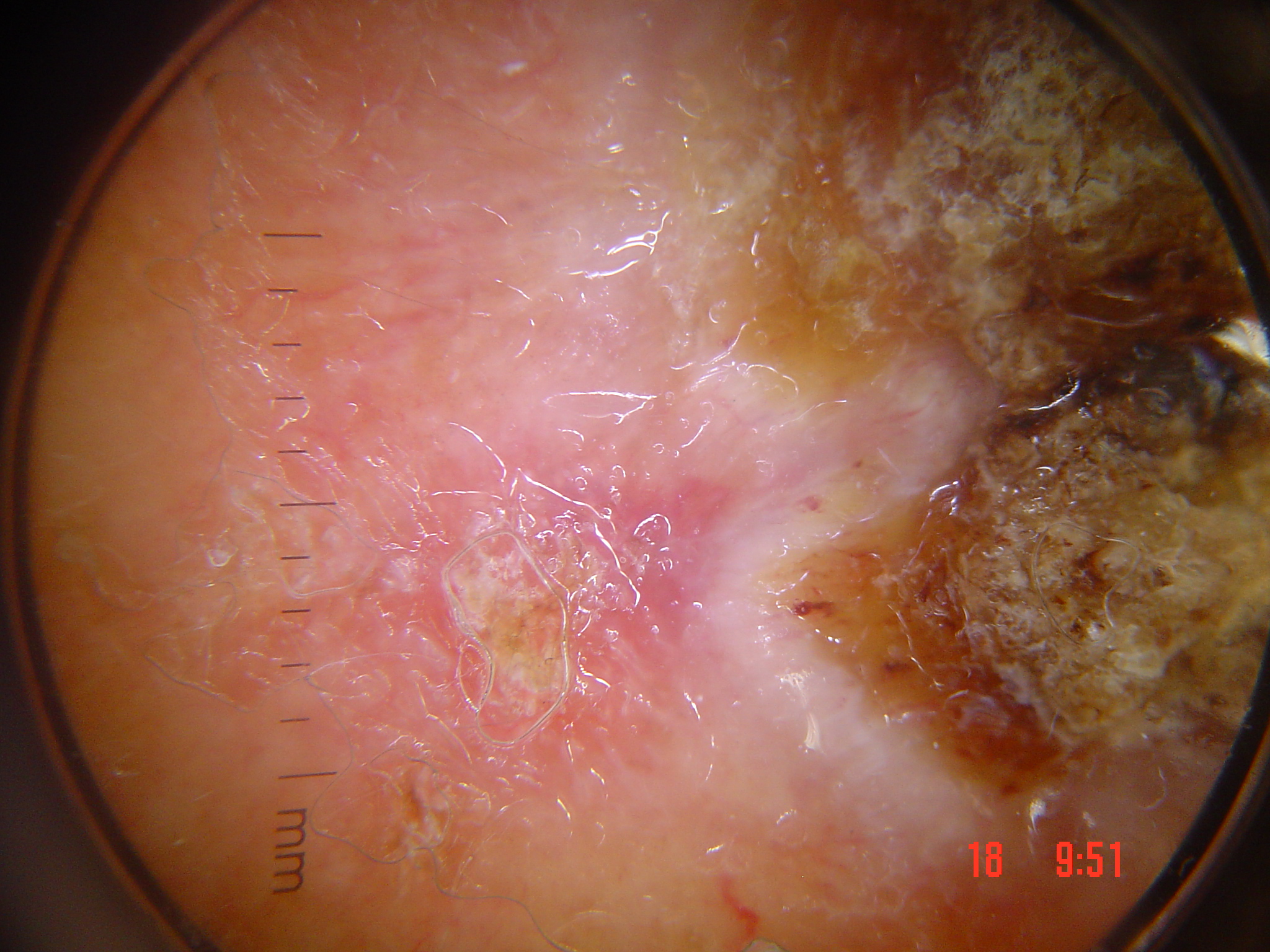– label — squamous cell carcinoma (biopsy-proven)